Collected as part of a research study, without a referral diagnosis · dermoscopy of a skin lesion · a female patient aged 67 — 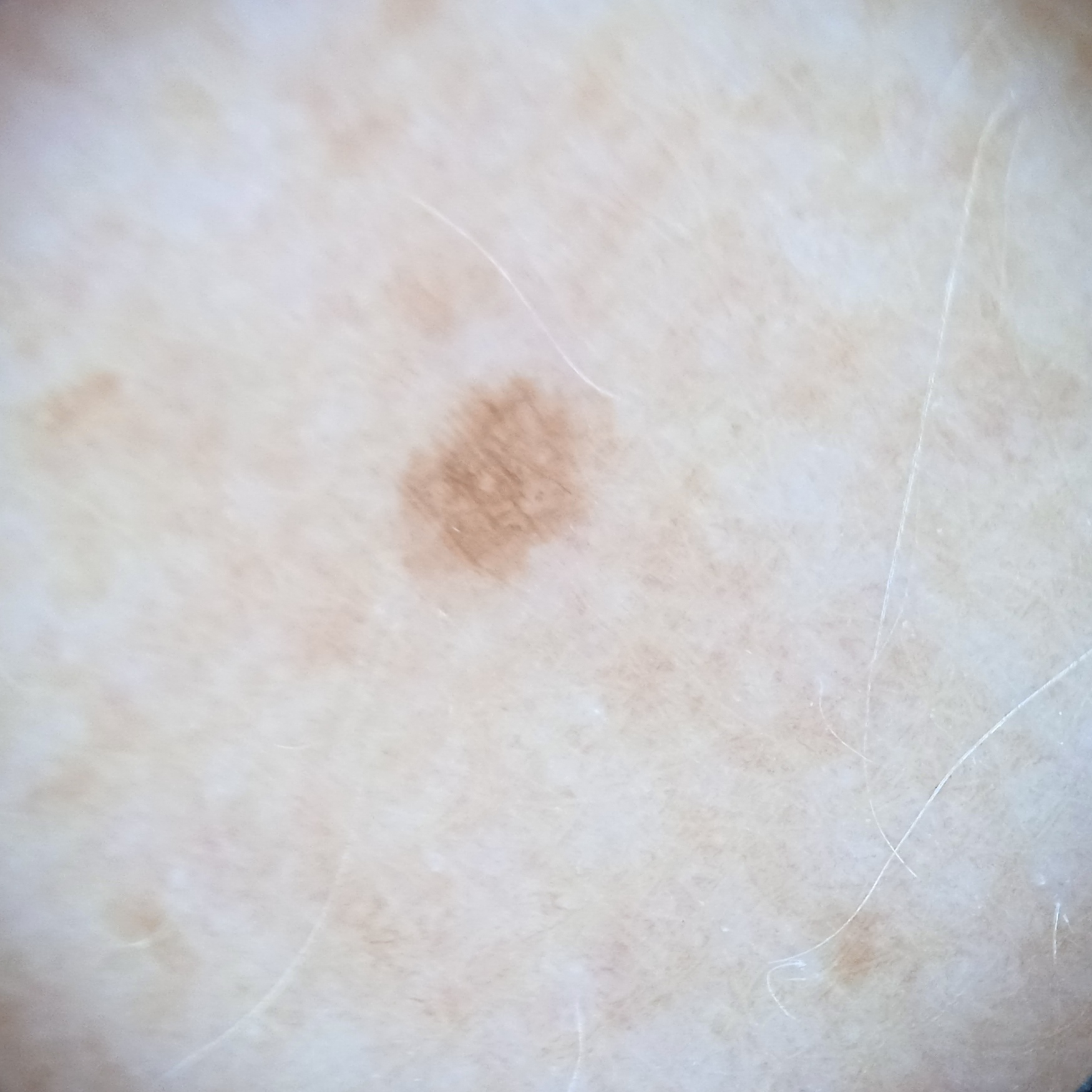Findings:
The lesion is on an arm. The lesion is about 2.3 mm across.
Conclusion:
The diagnostic impression was a melanocytic nevus.